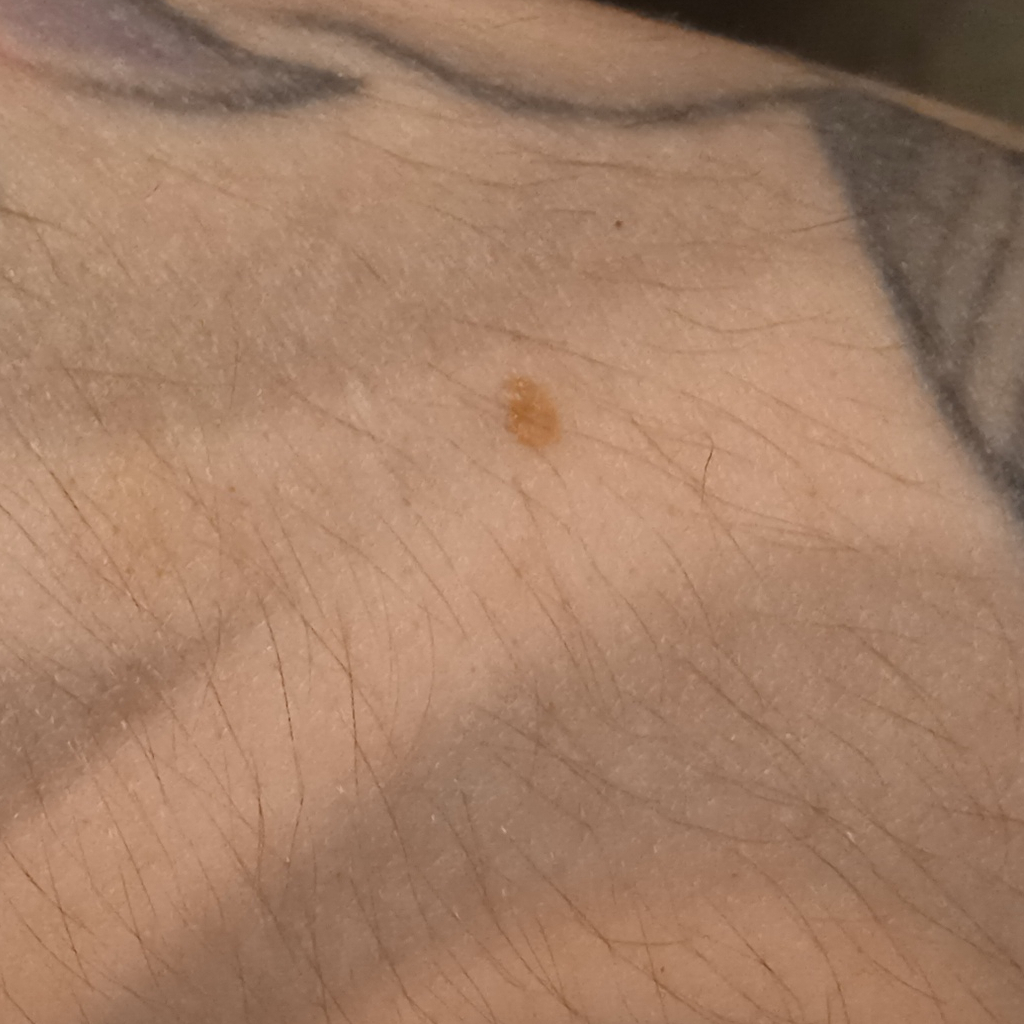Case summary:
A clinical photograph of a skin lesion. Collected as part of a research study, without a referral diagnosis.
Conclusion:
The four-dermatologist consensus diagnosis was a melanocytic nevus.